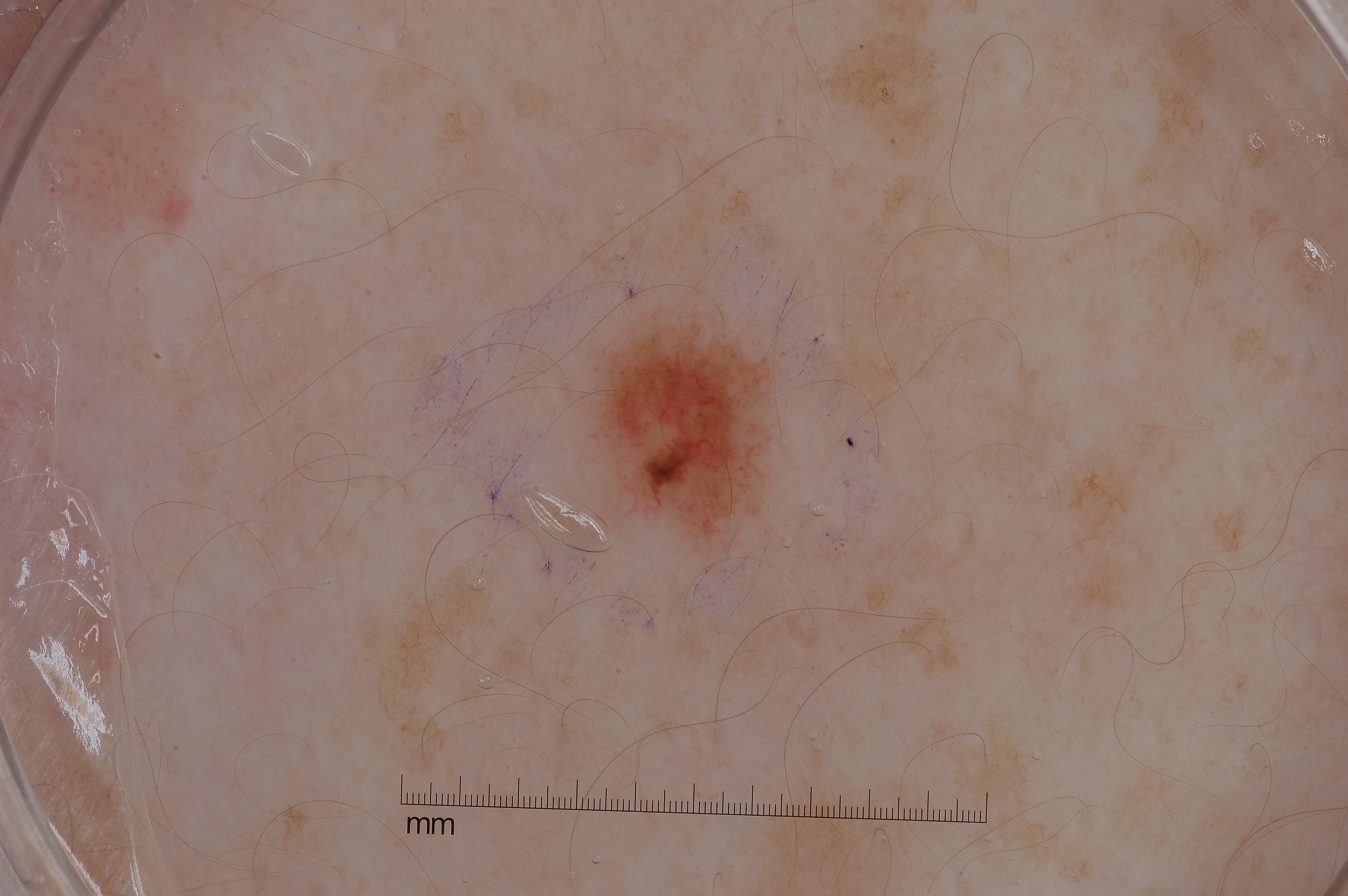A dermoscopic close-up of a skin lesion.
A female patient aged around 25.
Dermoscopic examination shows no pigment network, milia-like cysts, streaks, or negative network.
Lesion location: bbox=[590, 315, 769, 532].
The lesion was assessed as a melanocytic nevus, a benign skin lesion.